A dermatoscopic image of a skin lesion.
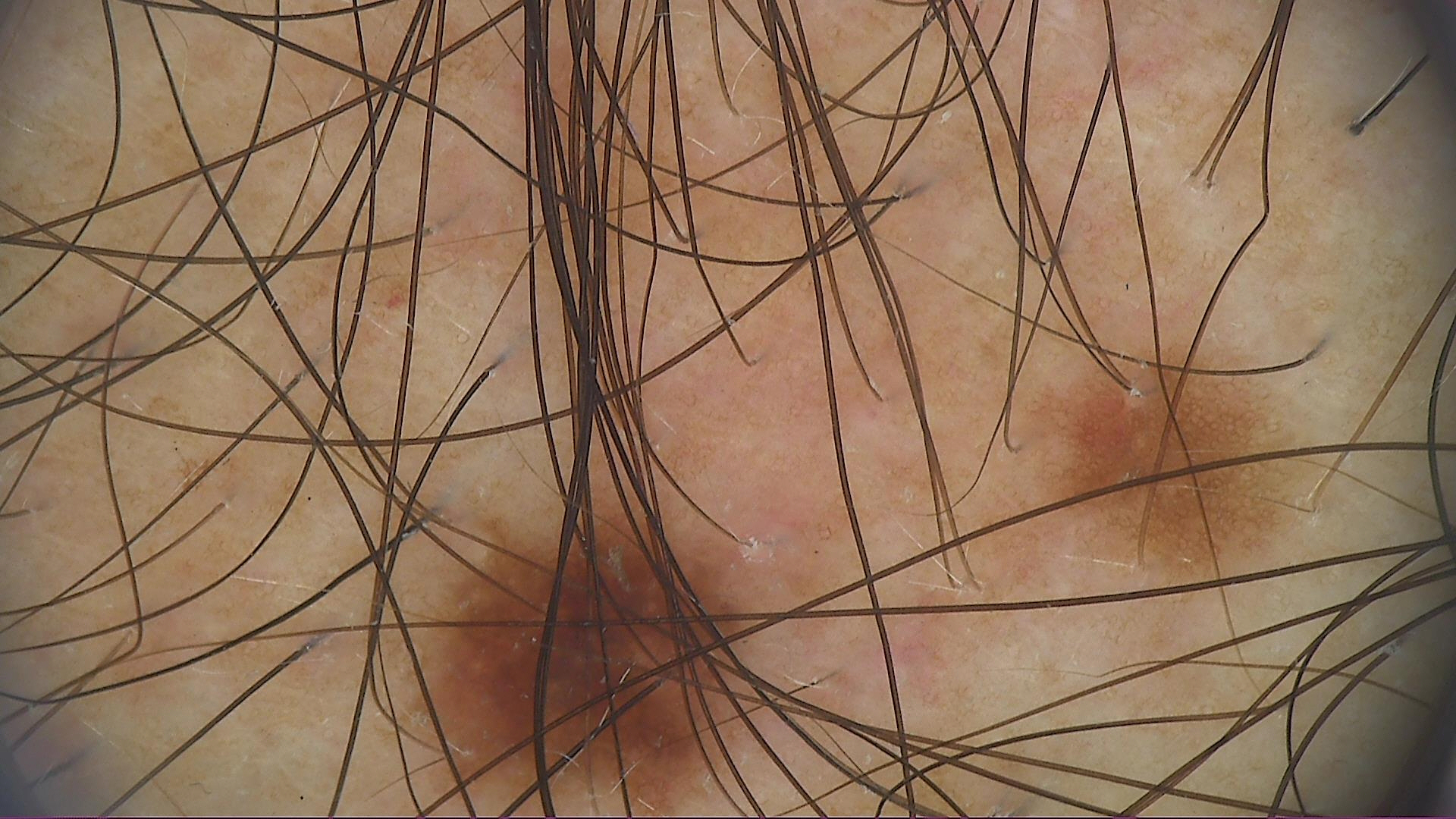{"diagnosis": {"name": "dysplastic junctional nevus", "code": "jd", "malignancy": "benign", "super_class": "melanocytic", "confirmation": "expert consensus"}}